Present for one to four weeks. Texture is reported as raised or bumpy. The photograph was taken at a distance. Located on the arm: 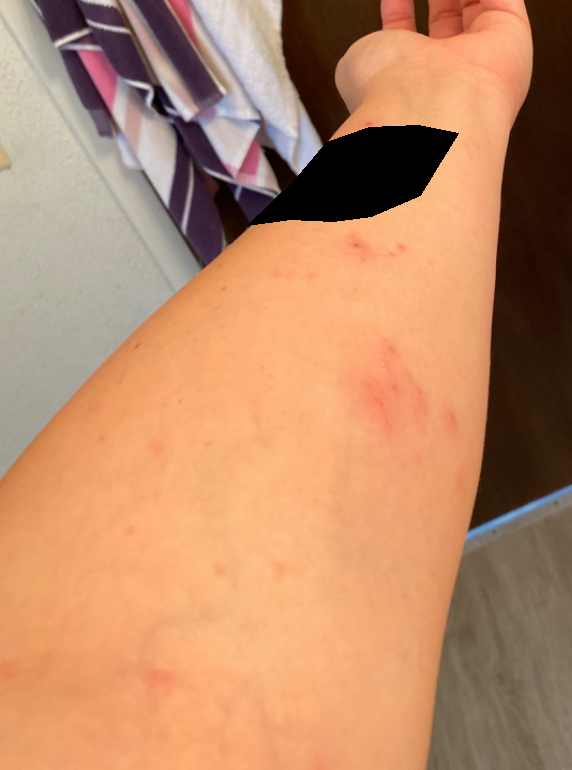Q: What is the dermatologist's impression?
A: the leading consideration is Allergic Contact Dermatitis; the differential also includes Herpes Zoster; also consider Eczema